The patient is a female aged 60–69 · the lesion involves the back of the torso, leg, arm and front of the torso · the photograph was taken at a distance — 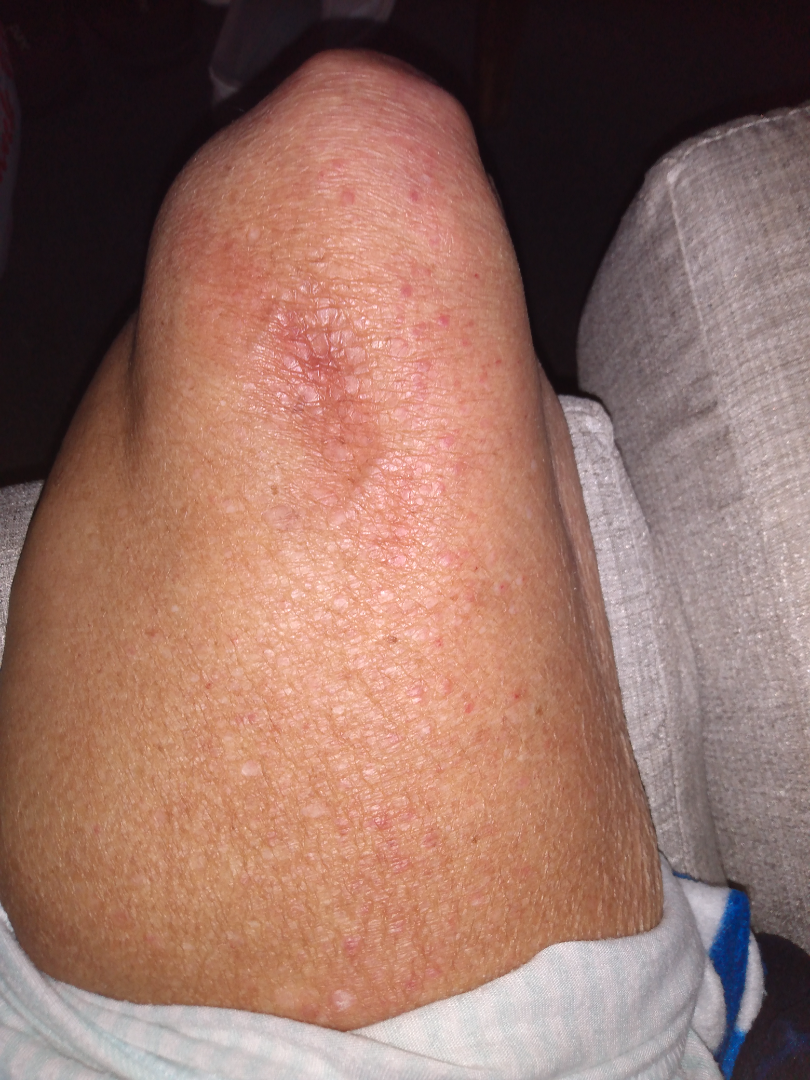The dermatologist could not determine a likely condition from the photograph alone. Symptoms reported: itching, pain and burning. Self-categorized by the patient as a rash. The contributor notes the condition has been present for one to four weeks. The contributor notes the lesion is raised or bumpy.